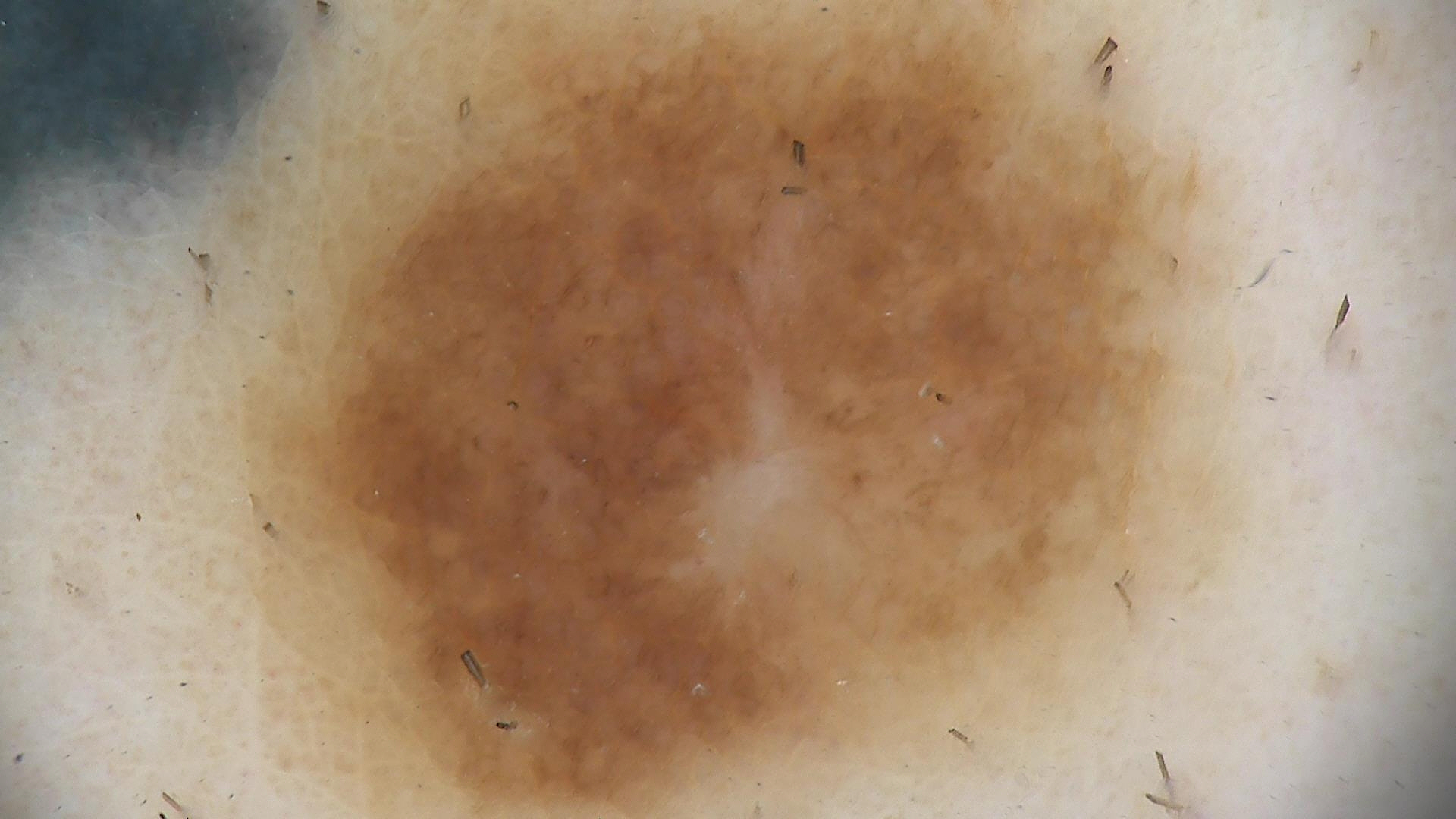Case:
– label · compound nevus (expert consensus)